The affected area is the leg · the photograph was taken at an angle · self-categorized by the patient as a rash · no associated systemic symptoms reported:
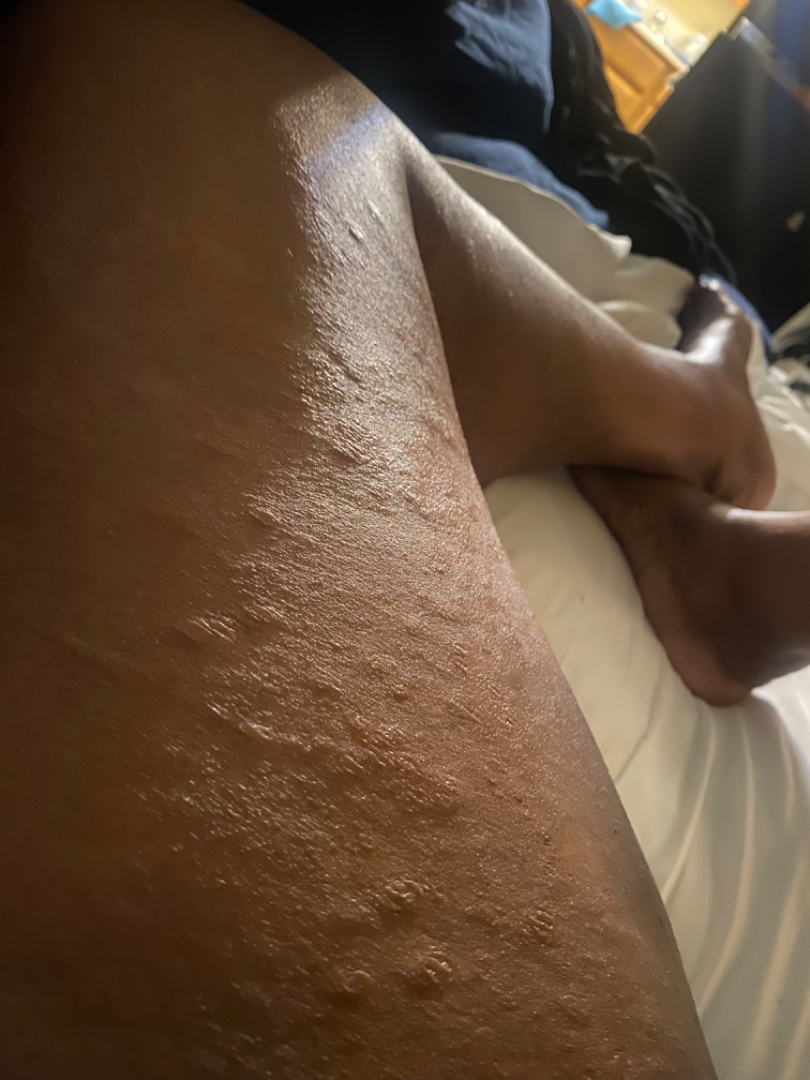Findings: A single dermatologist reviewed the case: the differential is split between Cutaneous T Cell Lymphoma, Psoriasis and Eczema.